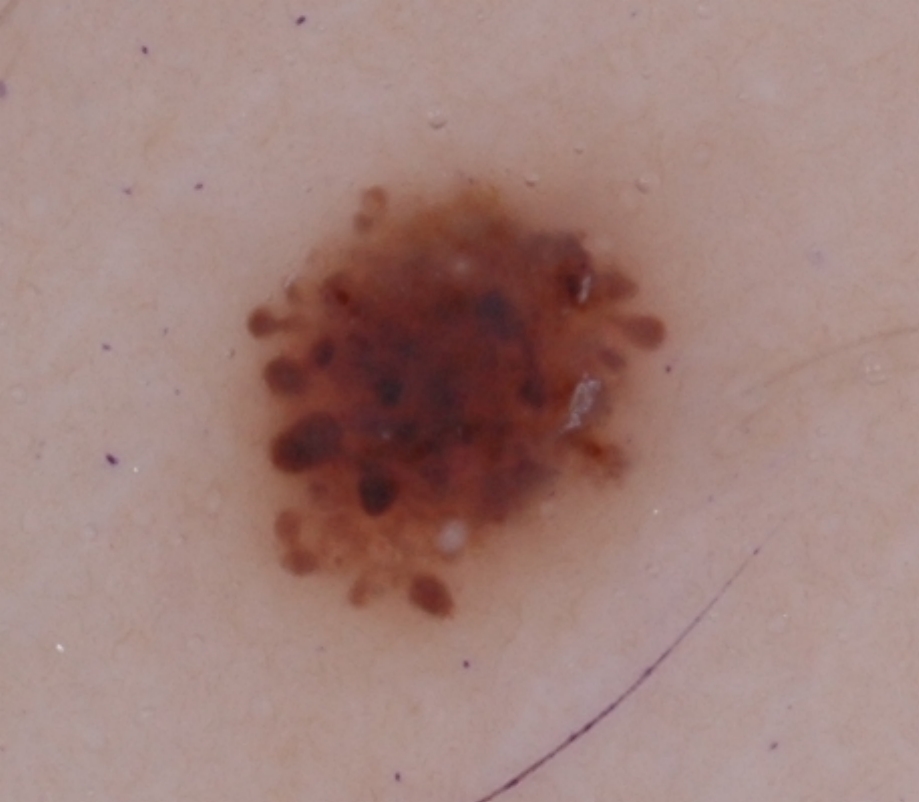A dermoscopic image of a skin lesion.
The lesion covers approximately 18% of the dermoscopic field.
The dermoscopic pattern shows globules and streaks, with no milia-like cysts, pigment network, or negative network.
The lesion is located at [245, 175, 666, 617].
The clinical diagnosis was a melanocytic nevus, a benign lesion.